A dermoscopy image of a single skin lesion: 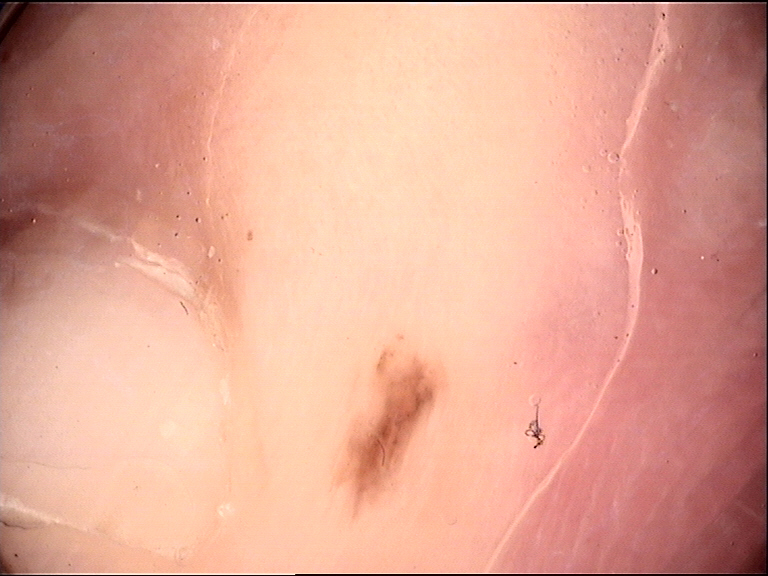diagnosis — acral dysplastic junctional nevus (expert consensus)